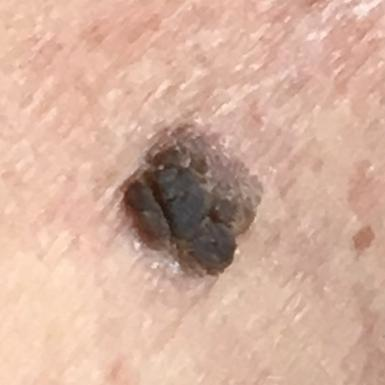A patient in their 80s.
A clinical close-up photograph of a skin lesion.
The lesion is located on the back.
The patient describes that the lesion has grown and is elevated.
Consistent with a seborrheic keratosis.